The lesion involves the back of the hand; the photograph is a close-up of the affected area; the contributor notes the lesion is rough or flaky and raised or bumpy; reported lesion symptoms include itching, pain, bothersome appearance and darkening: 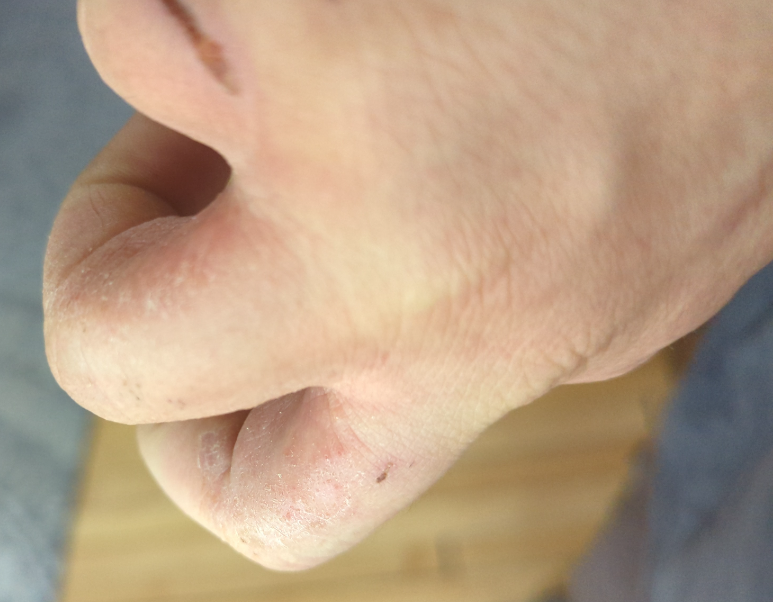assessment: ungradable on photographic review